A female patient approximately 65 years of age; a dermoscopy image of a single skin lesion.
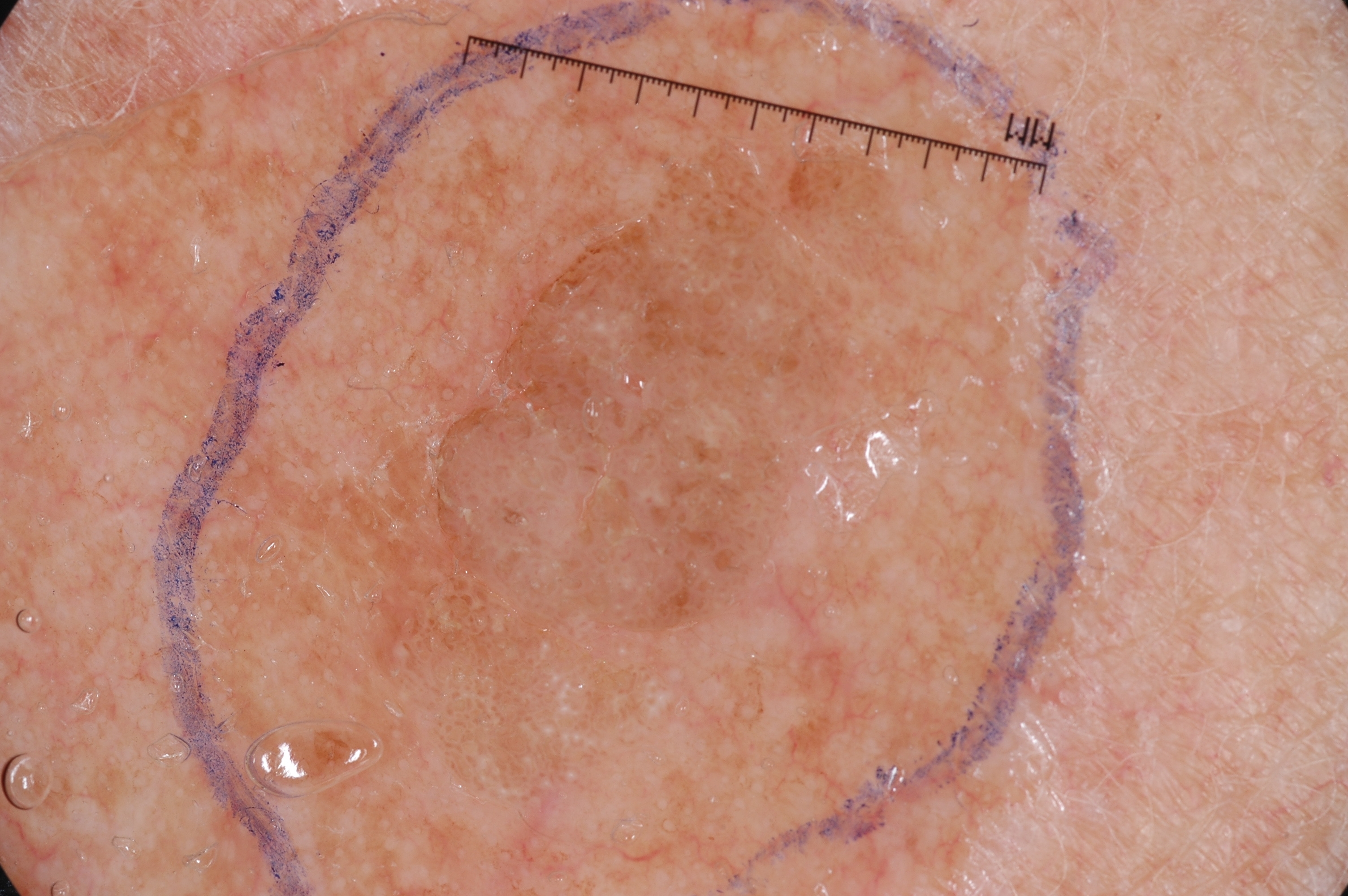lesion size: moderate
dermoscopic pattern: milia-like cysts
location: <box>382, 133, 910, 803</box>
assessment: a seborrheic keratosis, a benign skin lesion